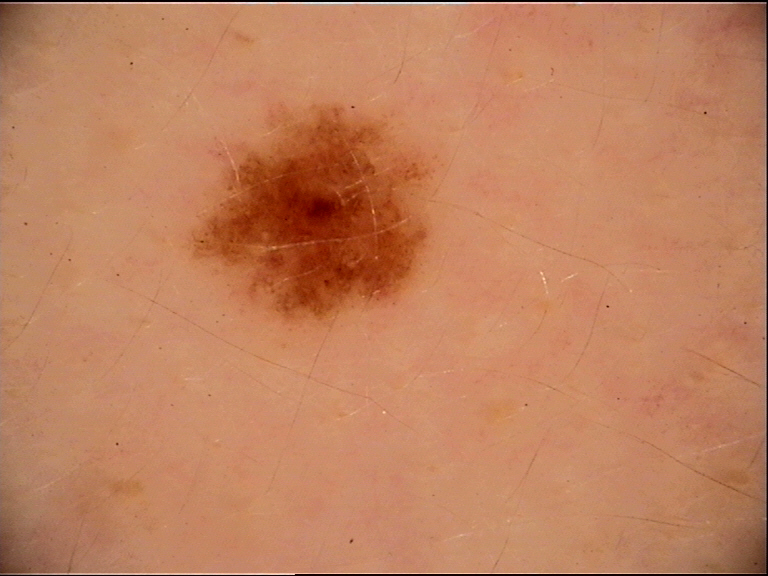modality: dermoscopy; class: dysplastic junctional nevus (expert consensus).